The contributor reports the lesion is raised or bumpy. Close-up view. The affected area is the arm. No constitutional symptoms were reported. Reported lesion symptoms include itching. The patient considered this a rash. The subject is a female aged 18–29: 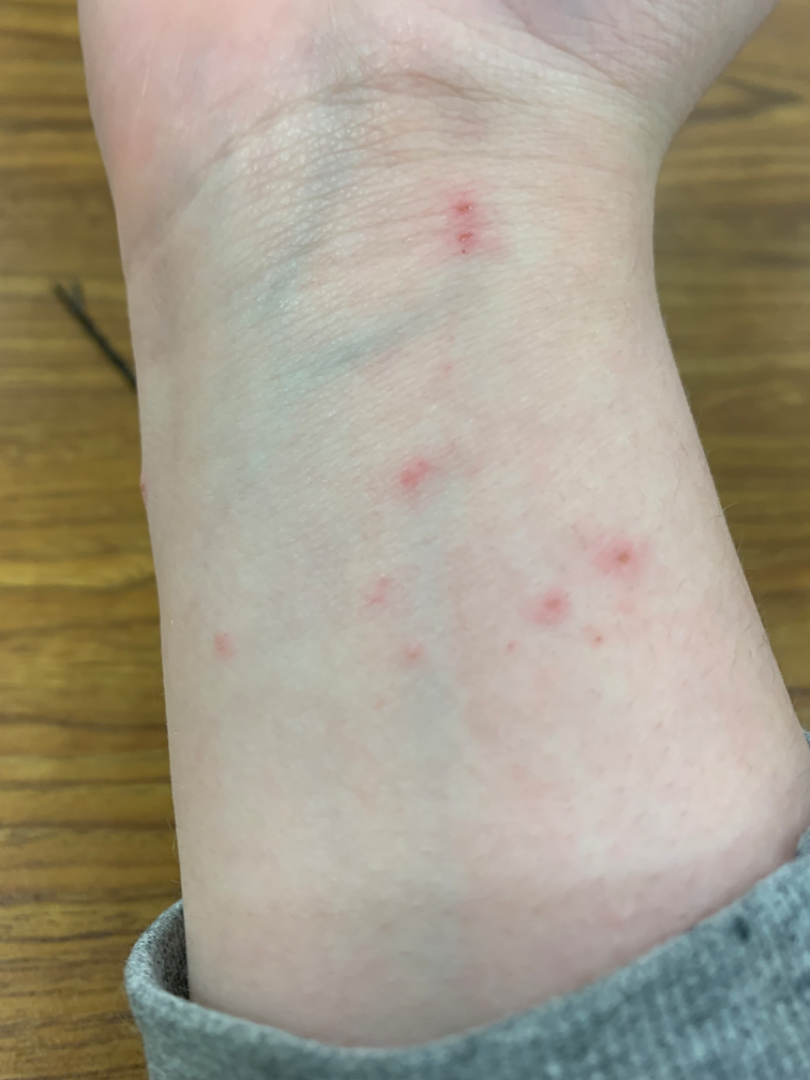assessment: not assessable.